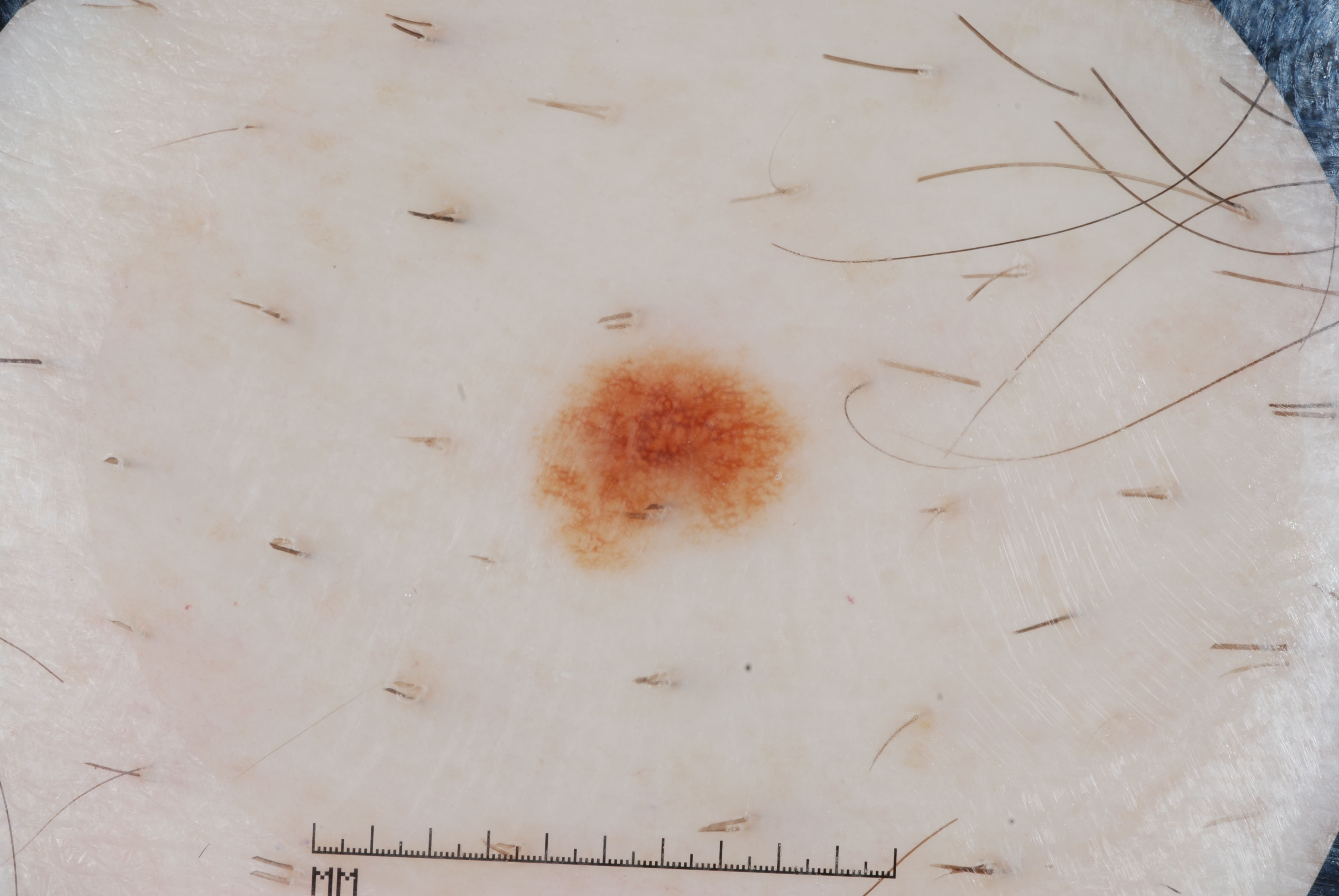A dermoscopic image of a skin lesion.
A male subject, aged 63-67.
The lesion occupies the region 544/343/795/567.
Dermoscopically, the lesion shows pigment network.
The lesion is small relative to the field of view.
The lesion was assessed as a melanocytic nevus, a benign lesion.